A female patient aged 64 · a moderate number of moles by the patient's own estimate · the patient reports a personal history of cancer and a family history of skin cancer: 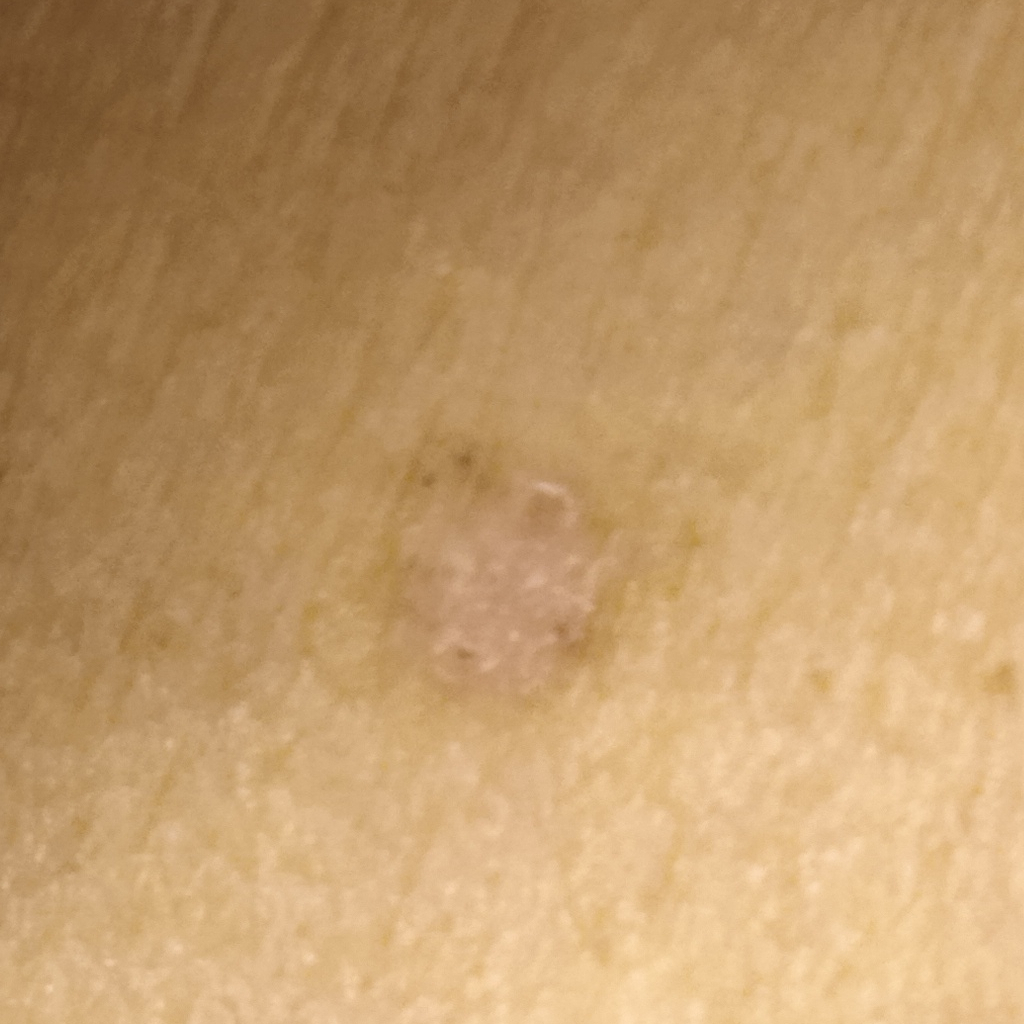{"lesion_location": "the torso", "diagnosis": {"name": "basal cell carcinoma", "malignancy": "malignant", "procedure": "punch biopsy", "tumor_thickness_mm": 0.6}}